A dermoscopic close-up of a skin lesion: 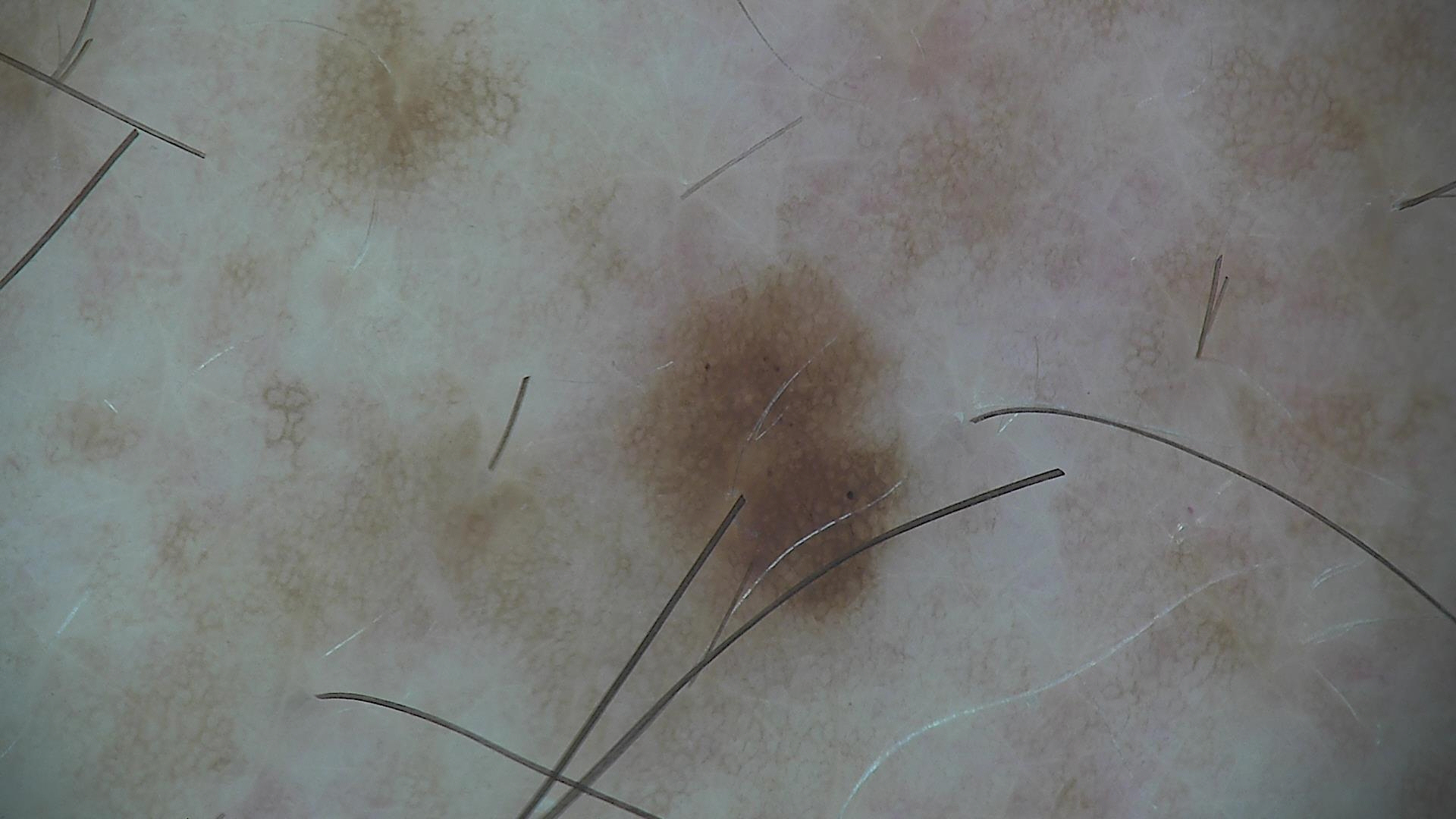class: dysplastic junctional nevus (expert consensus)